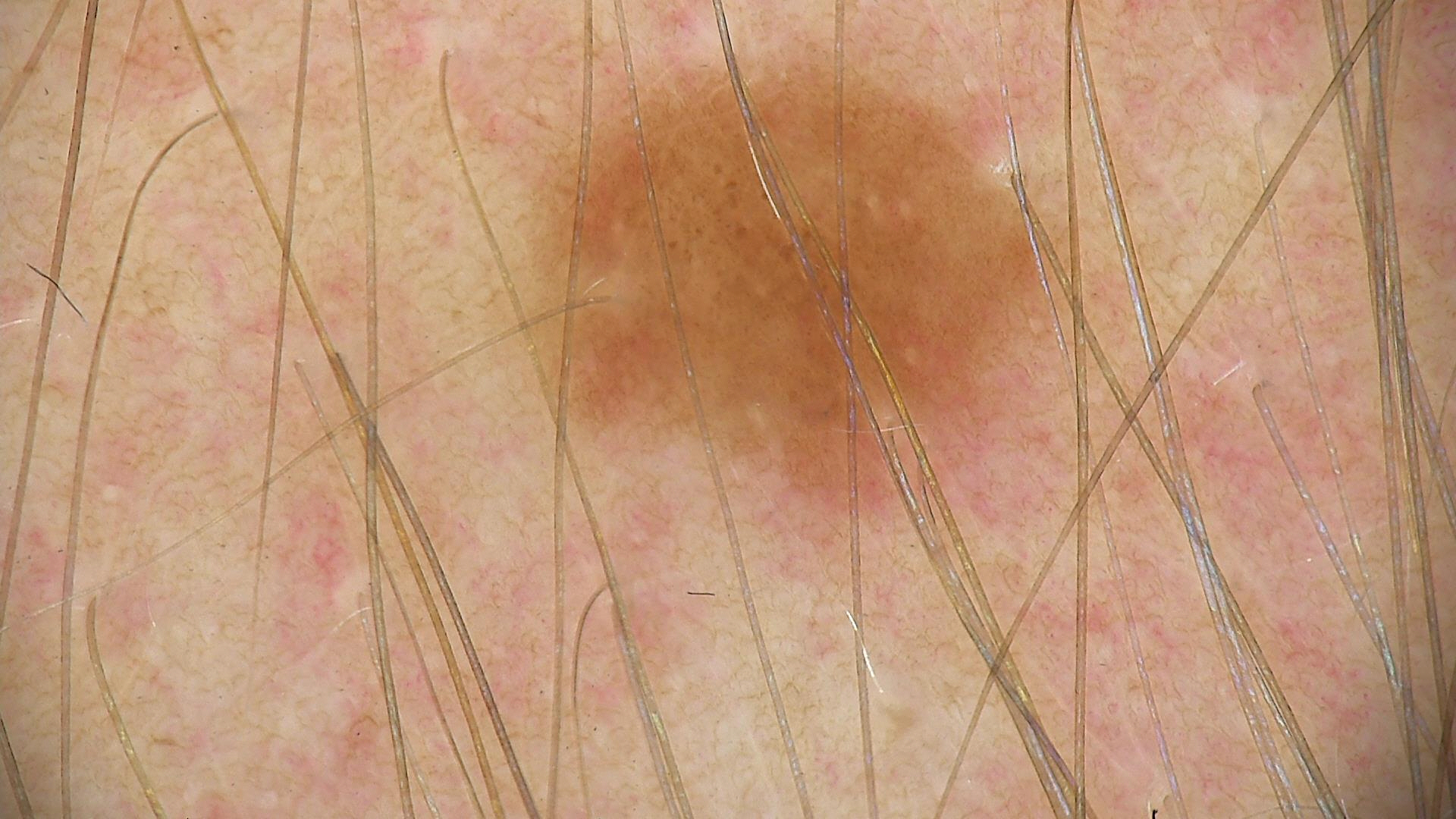{"diagnosis": {"name": "dysplastic junctional nevus", "code": "jd", "malignancy": "benign", "super_class": "melanocytic", "confirmation": "expert consensus"}}